A close-up photograph · the patient considered this a rash · the condition has been present for one to three months · the patient is female · the patient reports the lesion is rough or flaky · the affected area is the arm: 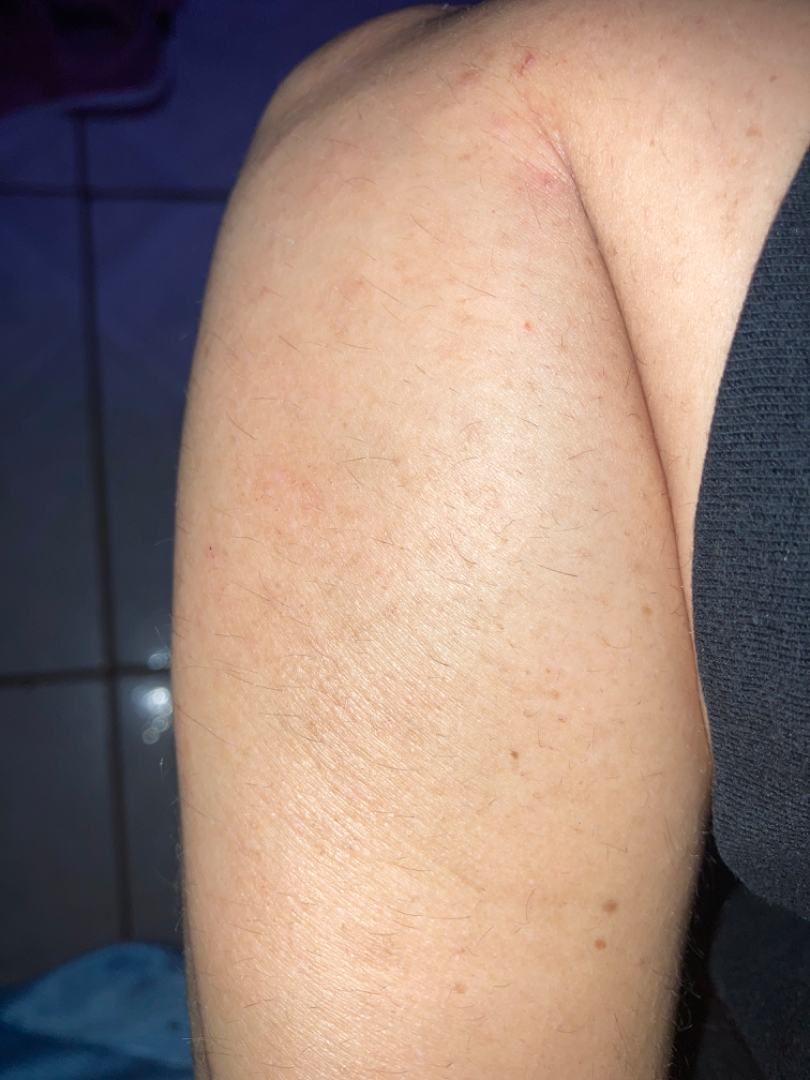– diagnostic considerations · Eczema (100%)